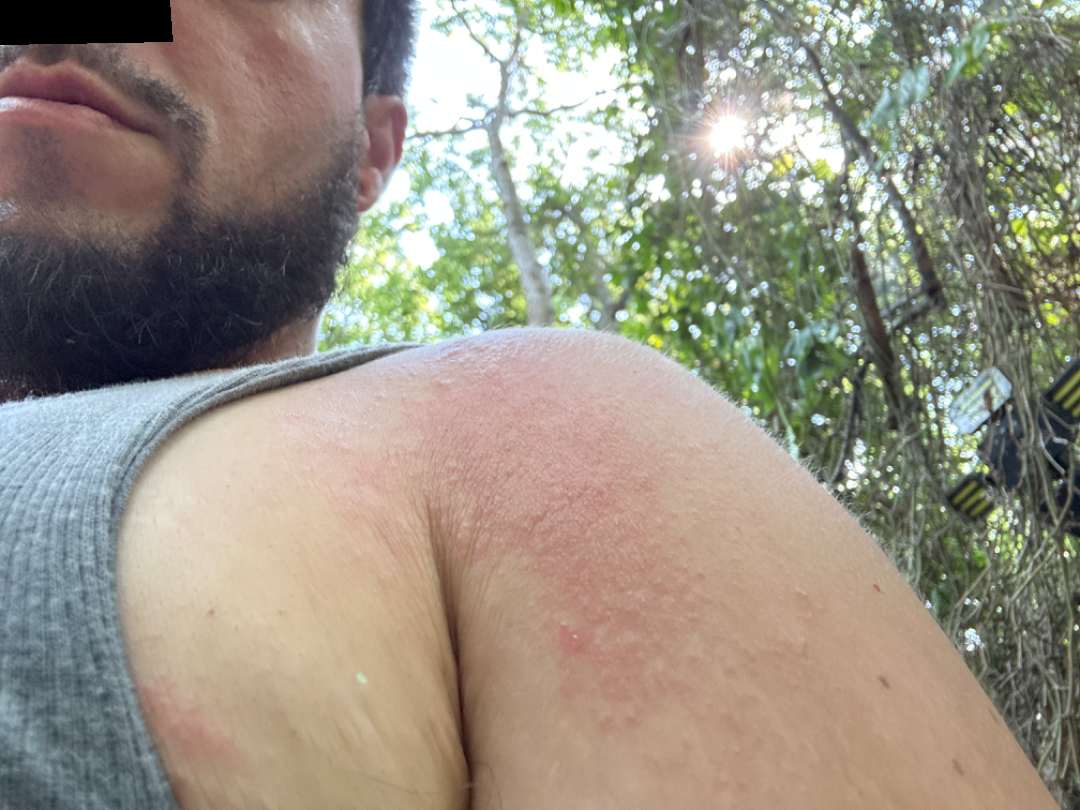The reviewing dermatologist's impression was: the differential, in no particular order, includes Acute dermatitis, NOS and Allergic Contact Dermatitis.